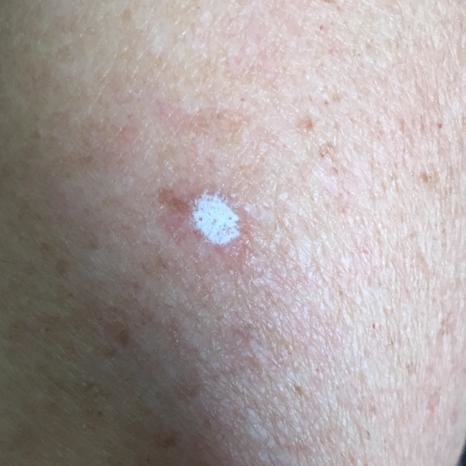subject = age 44; region = a forearm; impression = actinic keratosis (clinical consensus).